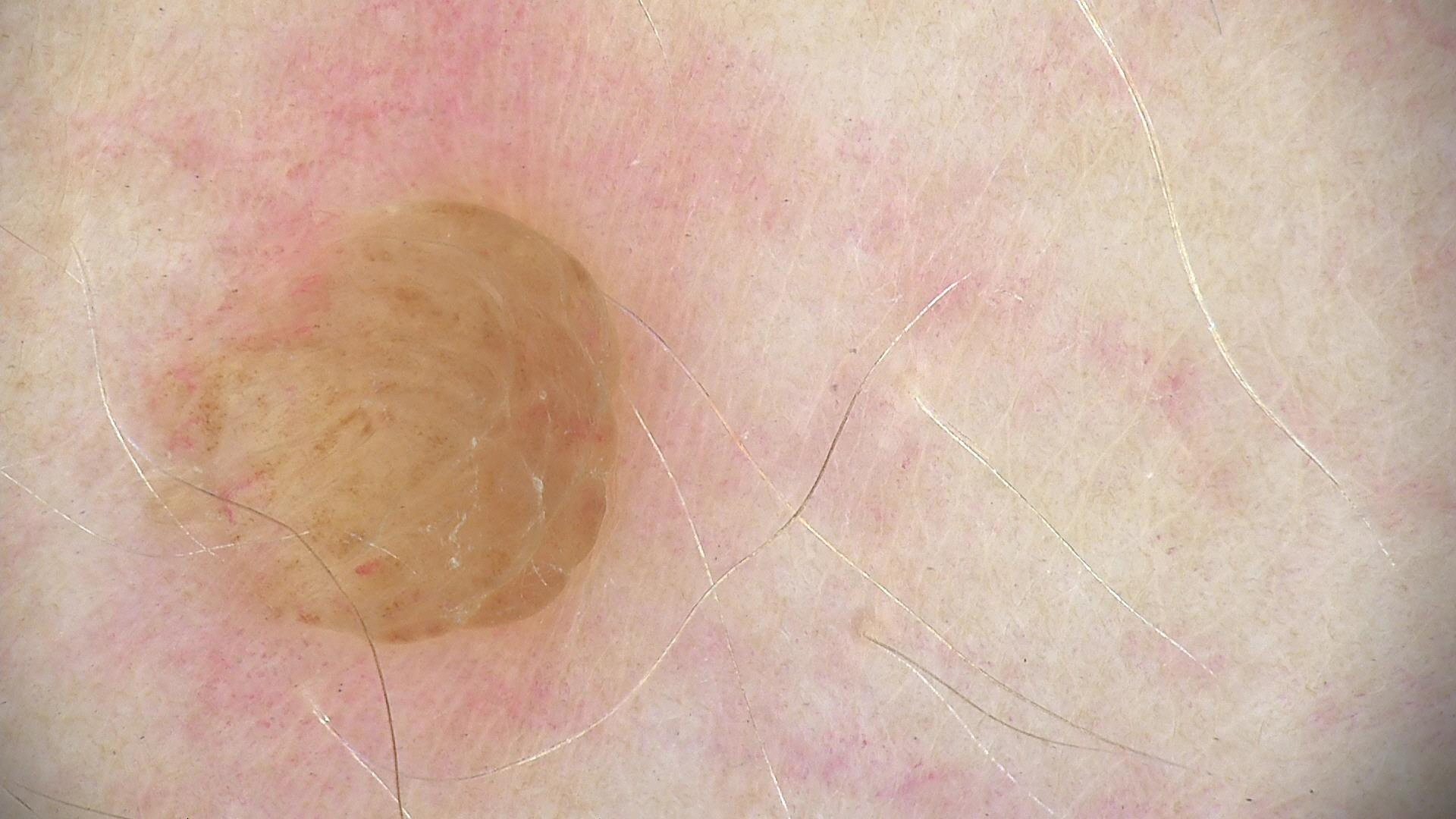Summary:
This is a banal lesion.
Impression:
Labeled as a dermal nevus.